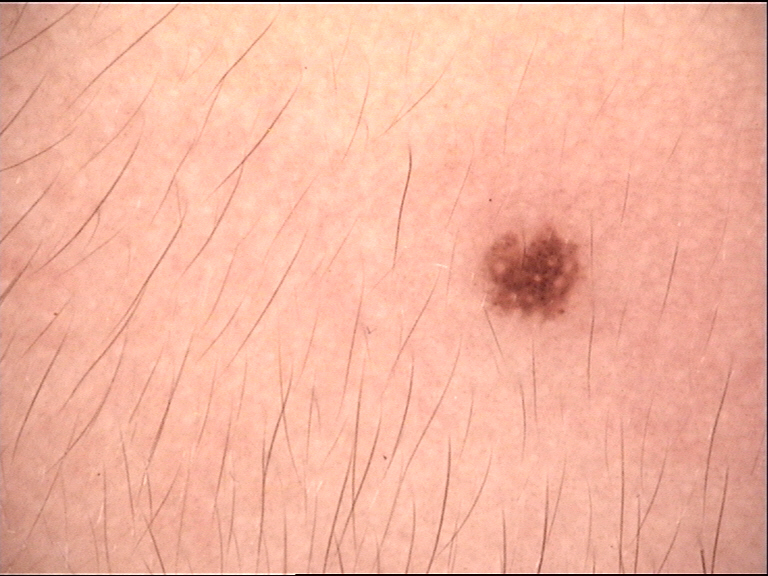Impression: Diagnosed as a Miescher nevus.